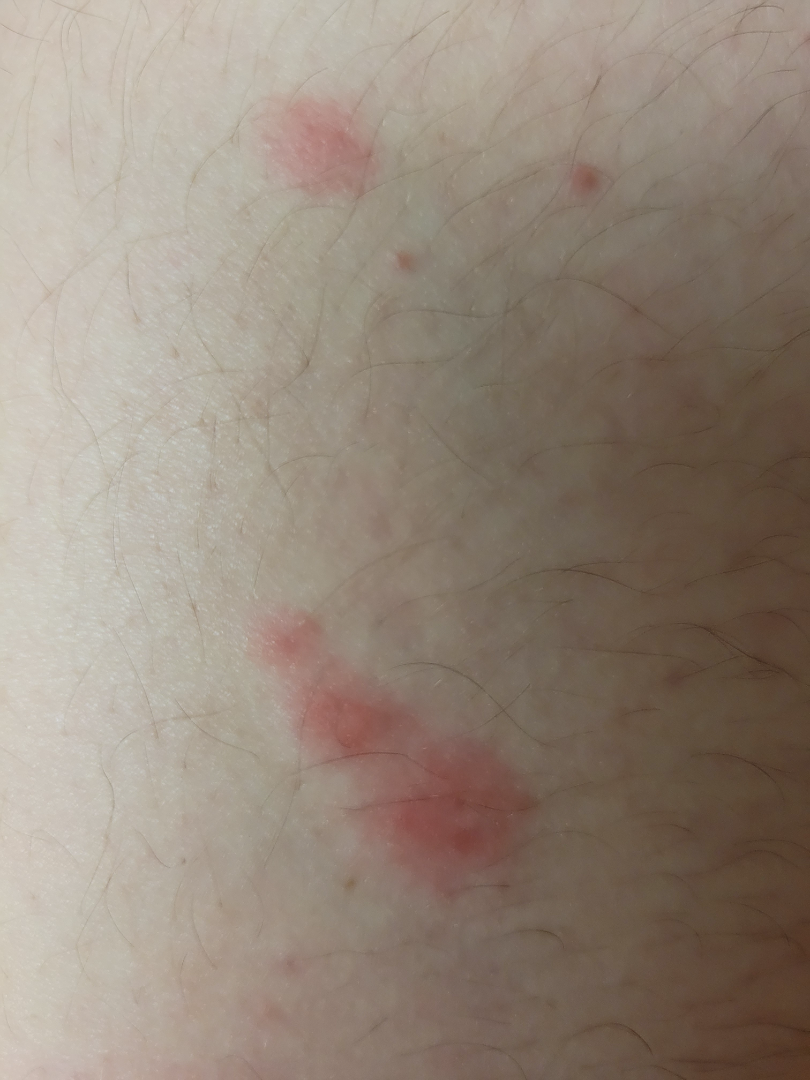{"body_site": "leg", "shot_type": "close-up", "differential": {"leading": ["Insect Bite"], "considered": ["Urticaria", "Allergic Contact Dermatitis"]}}